A male patient aged 83 or older — 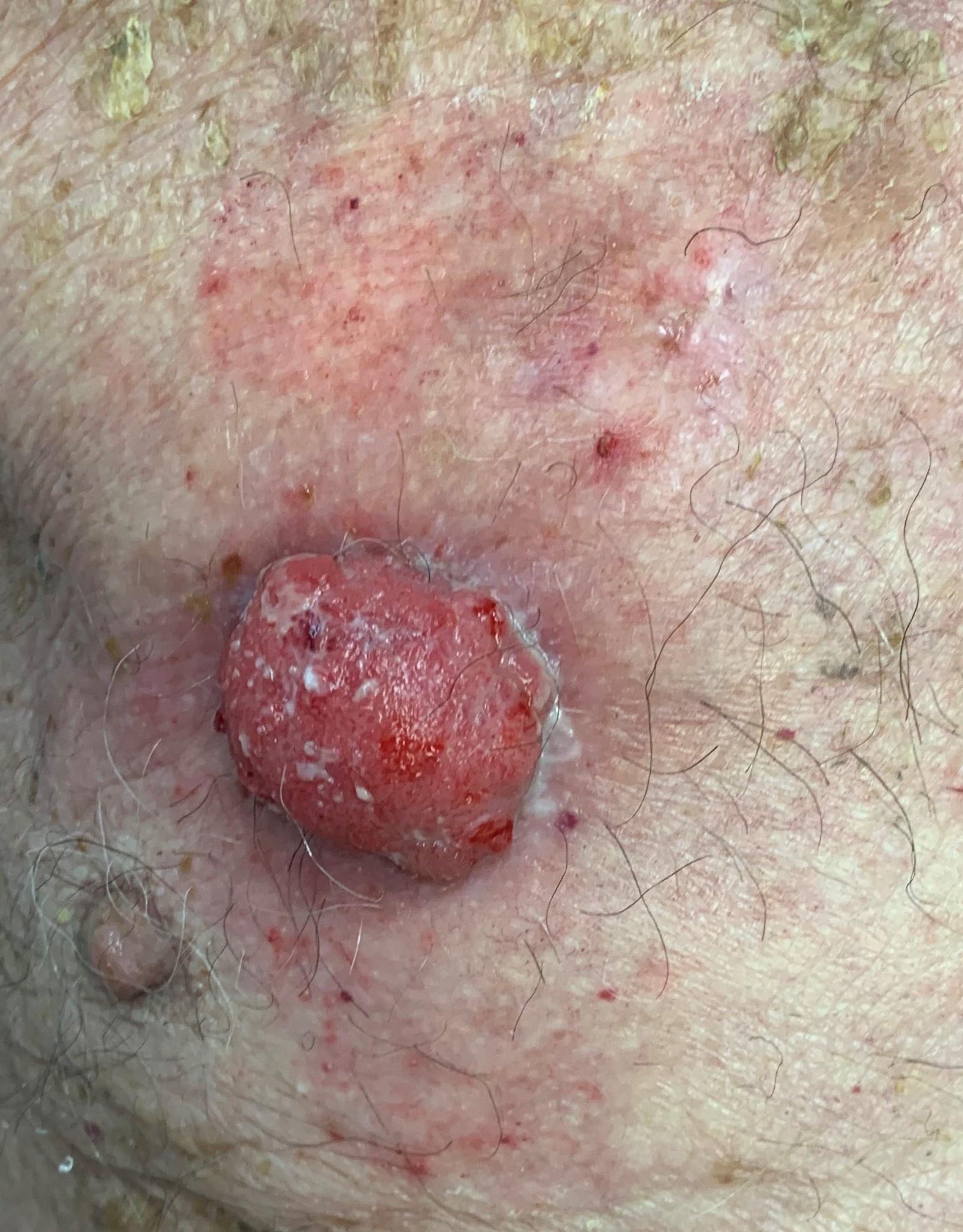Located on the anterior trunk.
Confirmed on histopathology as a squamous cell carcinoma.